A female subject approximately 70 years of age · a dermoscopic view of a skin lesion:
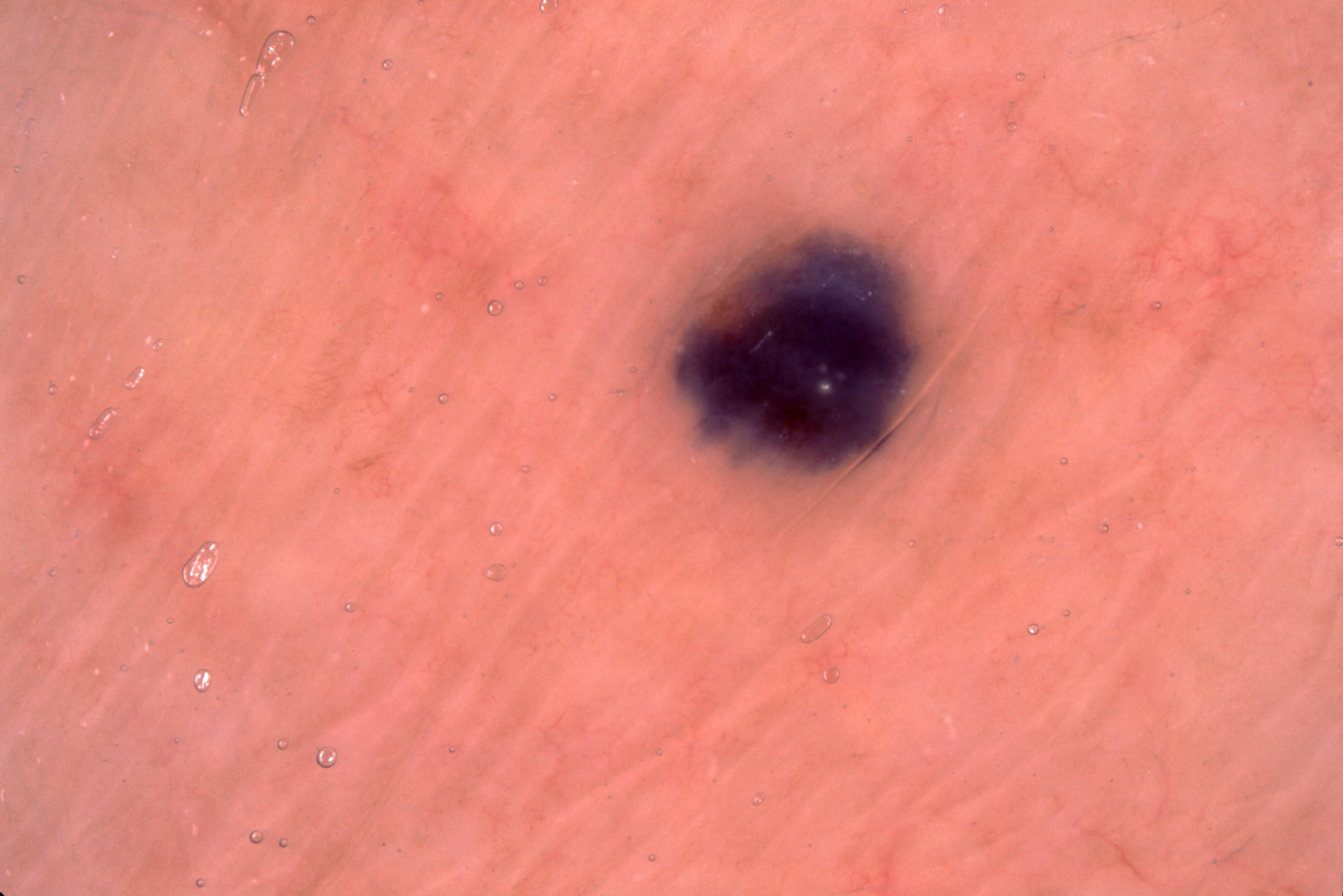  dermoscopic_features:
    present:
      - milia-like cysts
    absent:
      - negative network
      - pigment network
      - streaks
  lesion_extent:
    approx_field_fraction_pct: 4
  lesion_location:
    bbox_xyxy:
      - 667
      - 228
      - 930
      - 478
  diagnosis:
    name: melanocytic nevus
    malignancy: benign
    lineage: melanocytic
    provenance: clinical